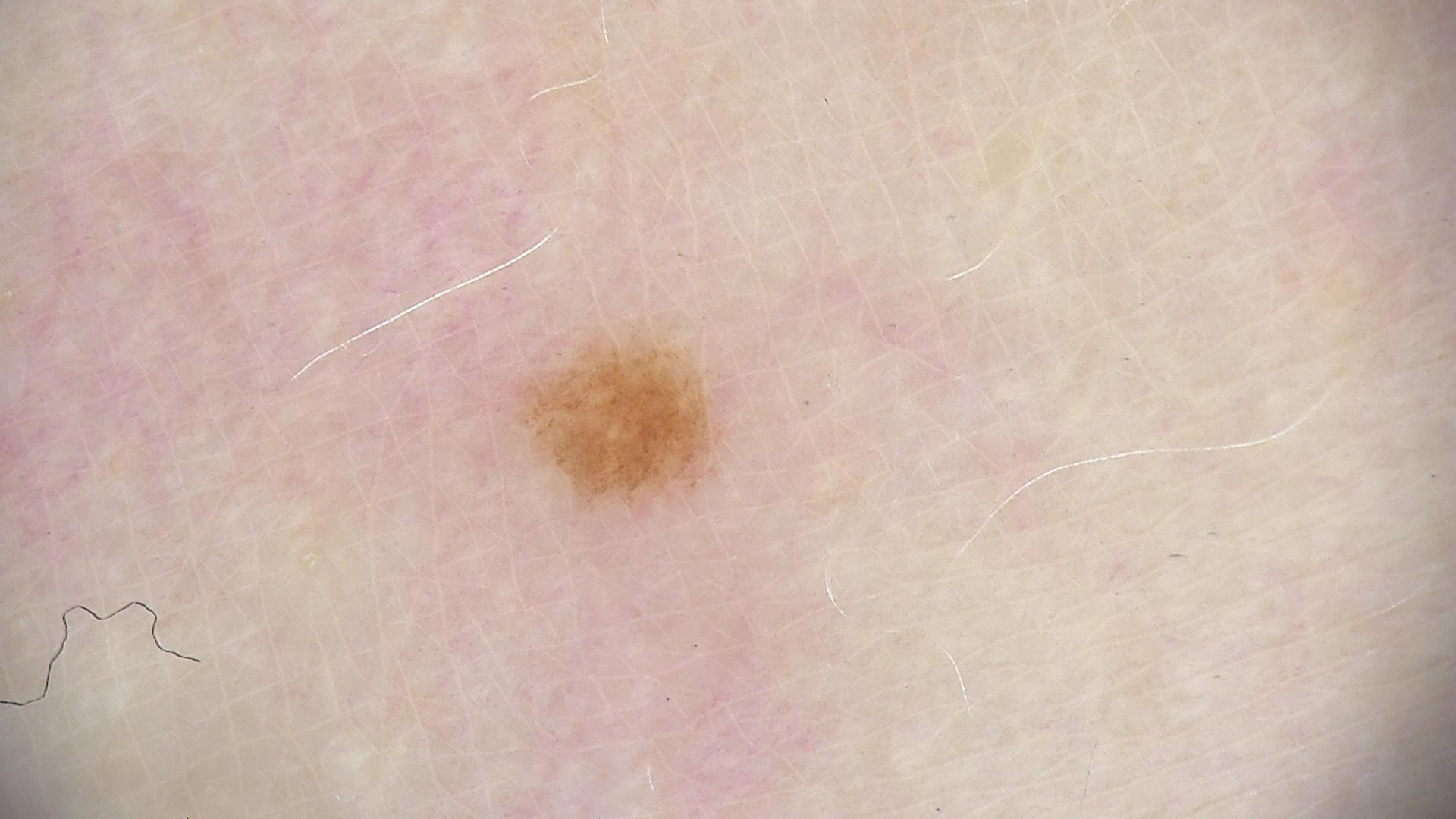modality: dermoscopy; diagnosis: dysplastic junctional nevus (expert consensus).